Male contributor, age 30–39. The affected area is the back of the torso. An image taken at an angle: 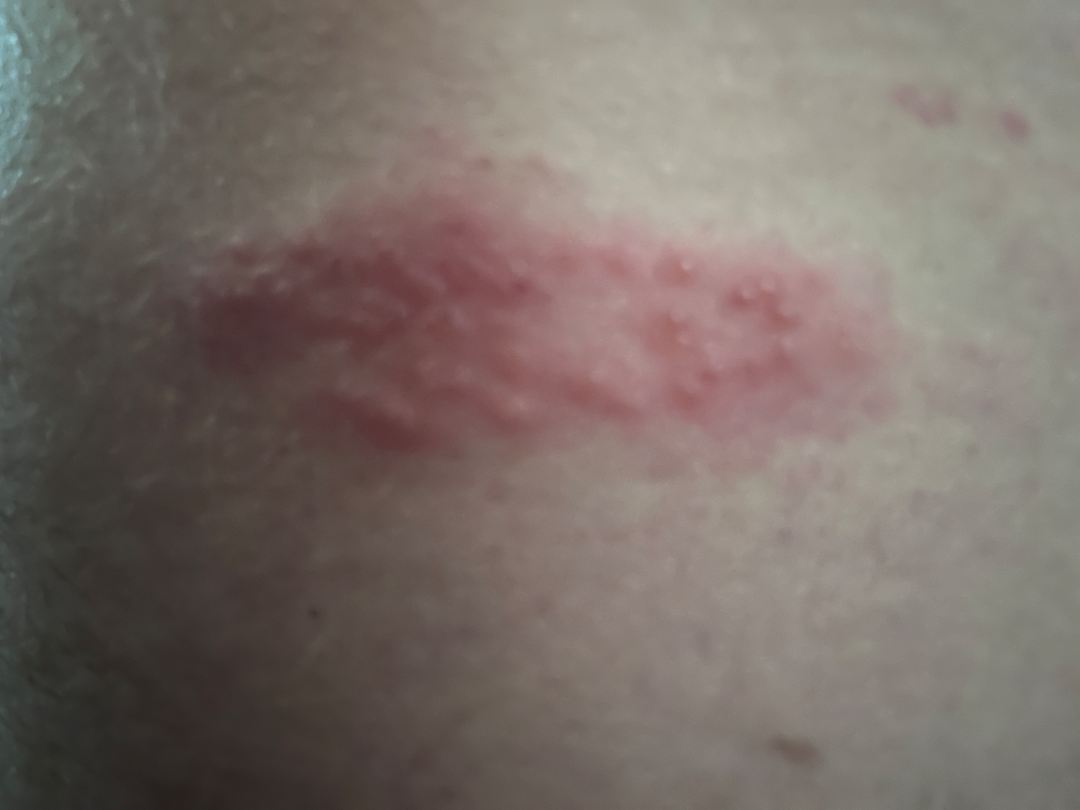Impression: One reviewing dermatologist: most consistent with Herpes Zoster; also on the differential is Acute dermatitis, NOS.